A male patient approximately 55 years of age. A dermoscopic view of a skin lesion:
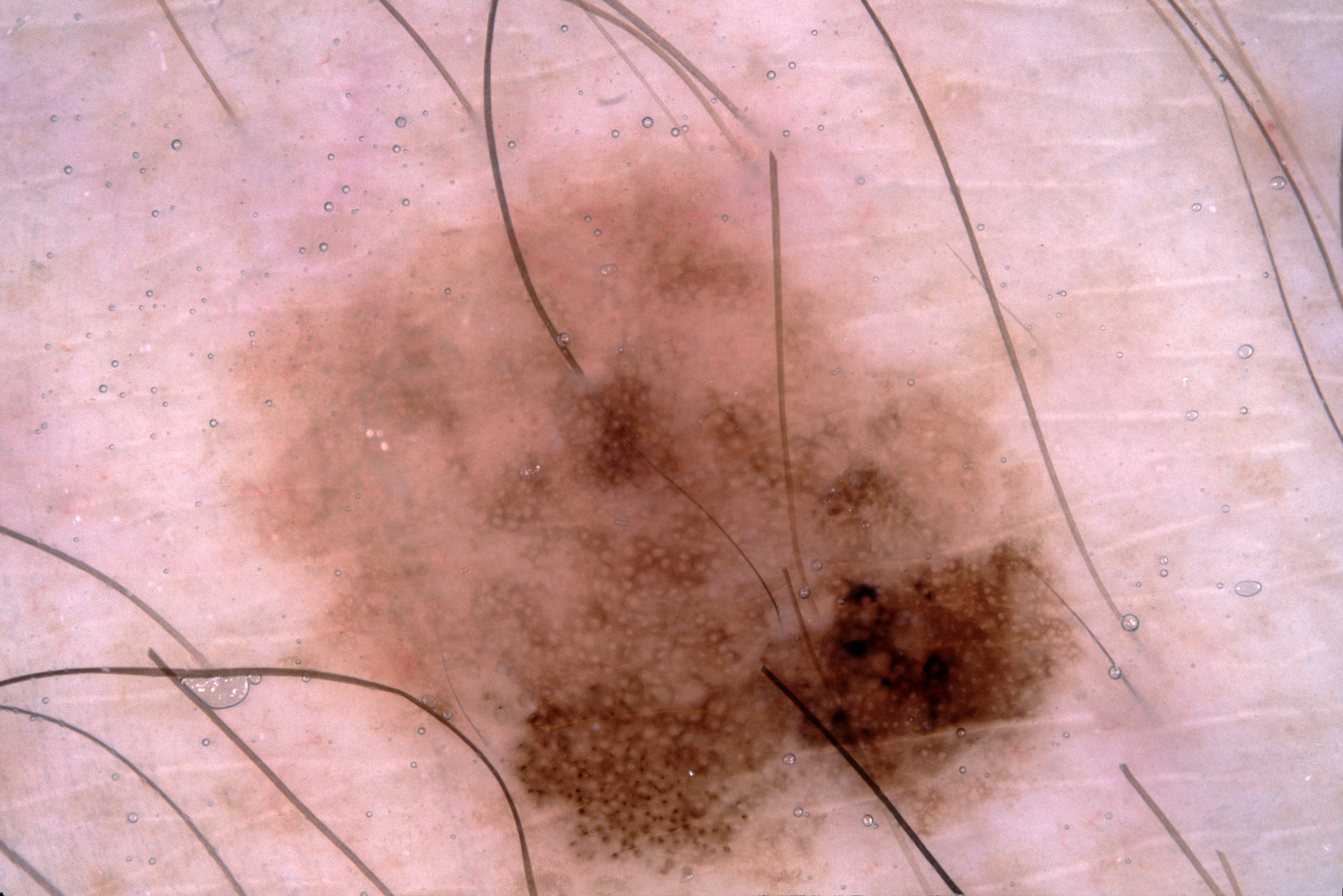extent = ~36% of the field
bounding box = bbox(241, 154, 1081, 882)
dermoscopic findings = pigment network; absent: negative network, milia-like cysts, and streaks
assessment = a melanoma